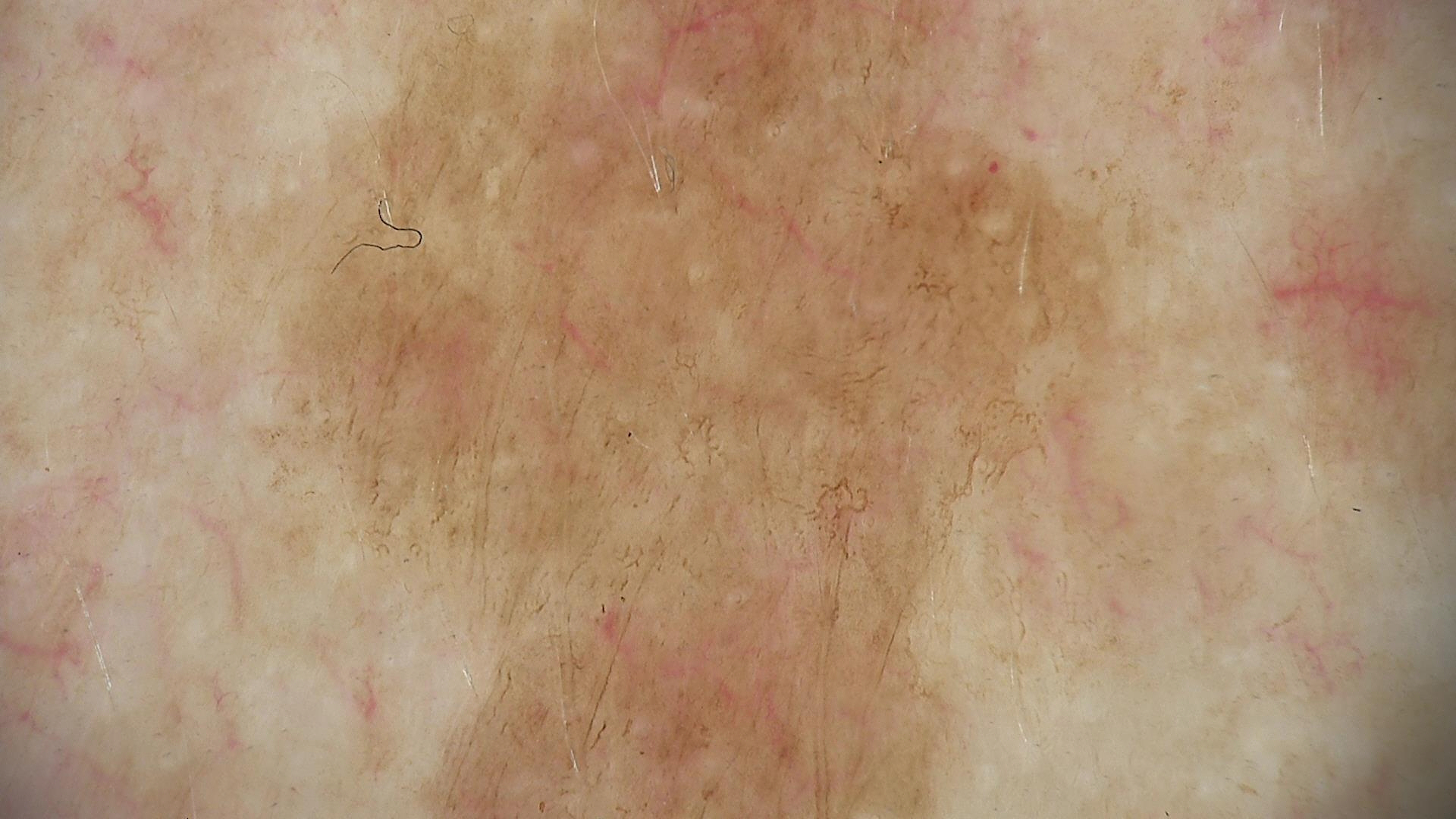Case:
A dermoscopic photograph of a skin lesion.
Conclusion:
Classified as a keratinocytic, benign lesion — a seborrheic keratosis.